A dermoscopic photograph of a skin lesion: 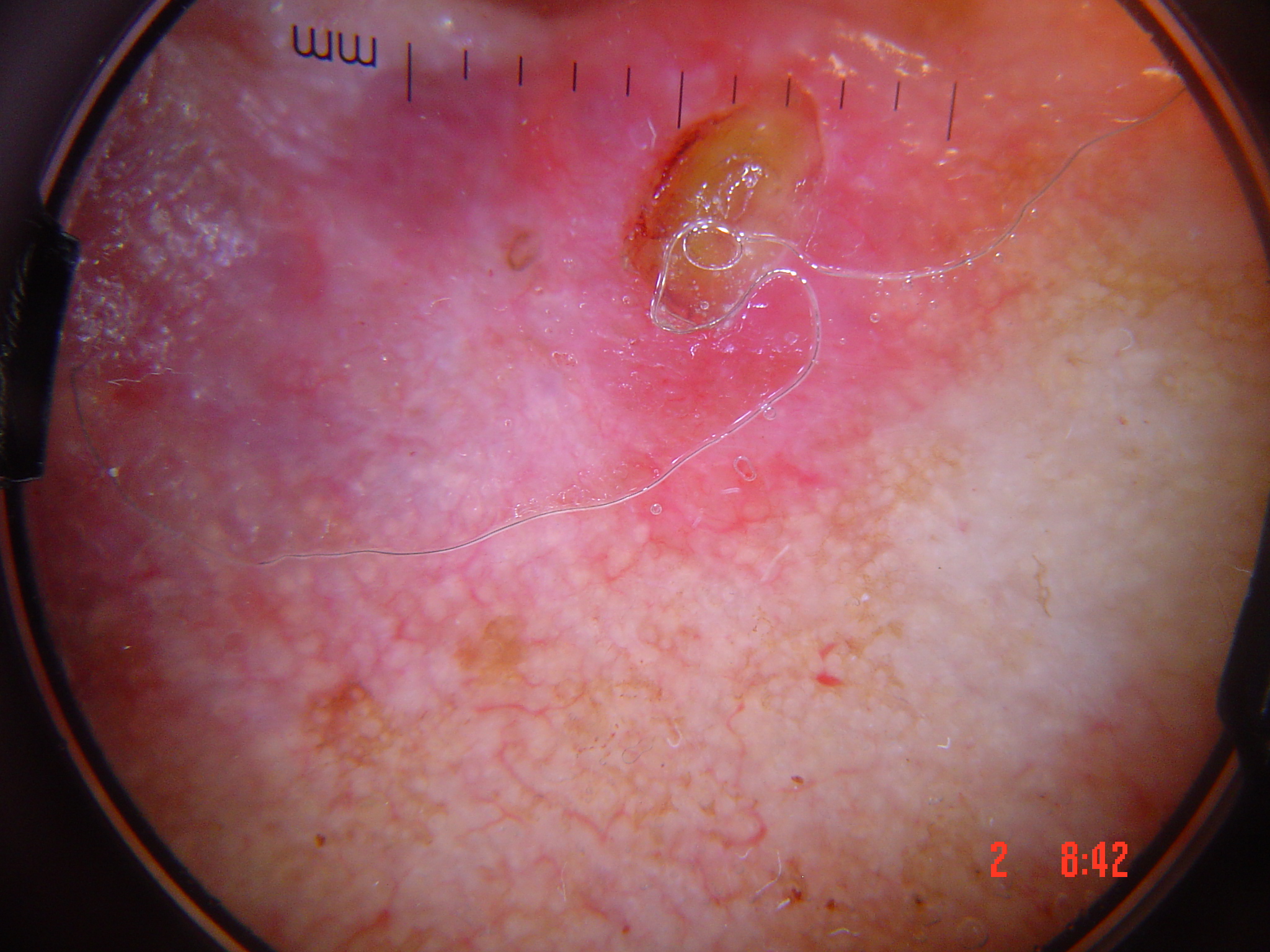This is a keratinocytic lesion.
Histopathology confirmed a squamous cell carcinoma.